The contributor is a male aged 30–39. The patient reports the lesion is raised or bumpy. The patient reports enlargement, bothersome appearance and itching. Located on the back of the hand and arm. This image was taken at an angle: 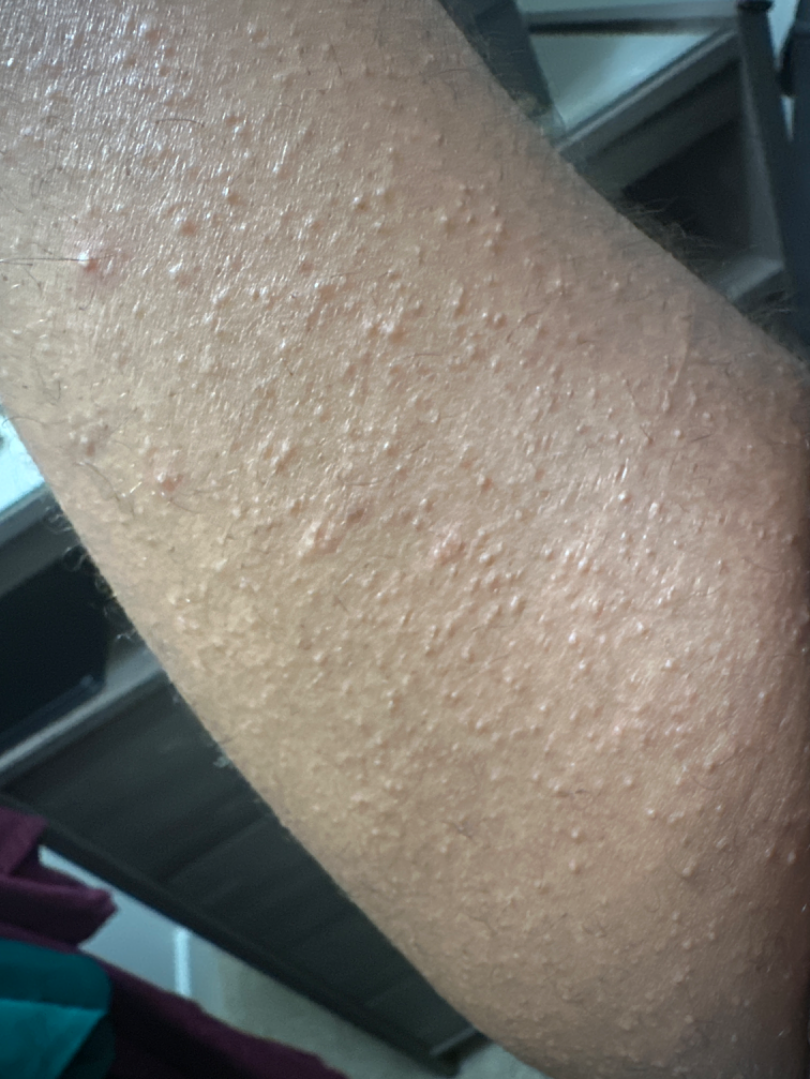Favoring Keratosis pilaris; with consideration of Miliaria.